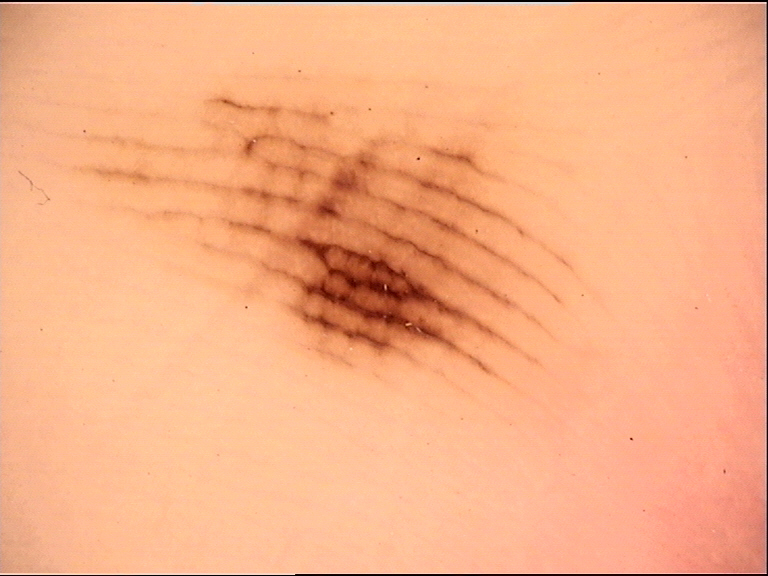The diagnostic label was a banal lesion — an acral junctional nevus.